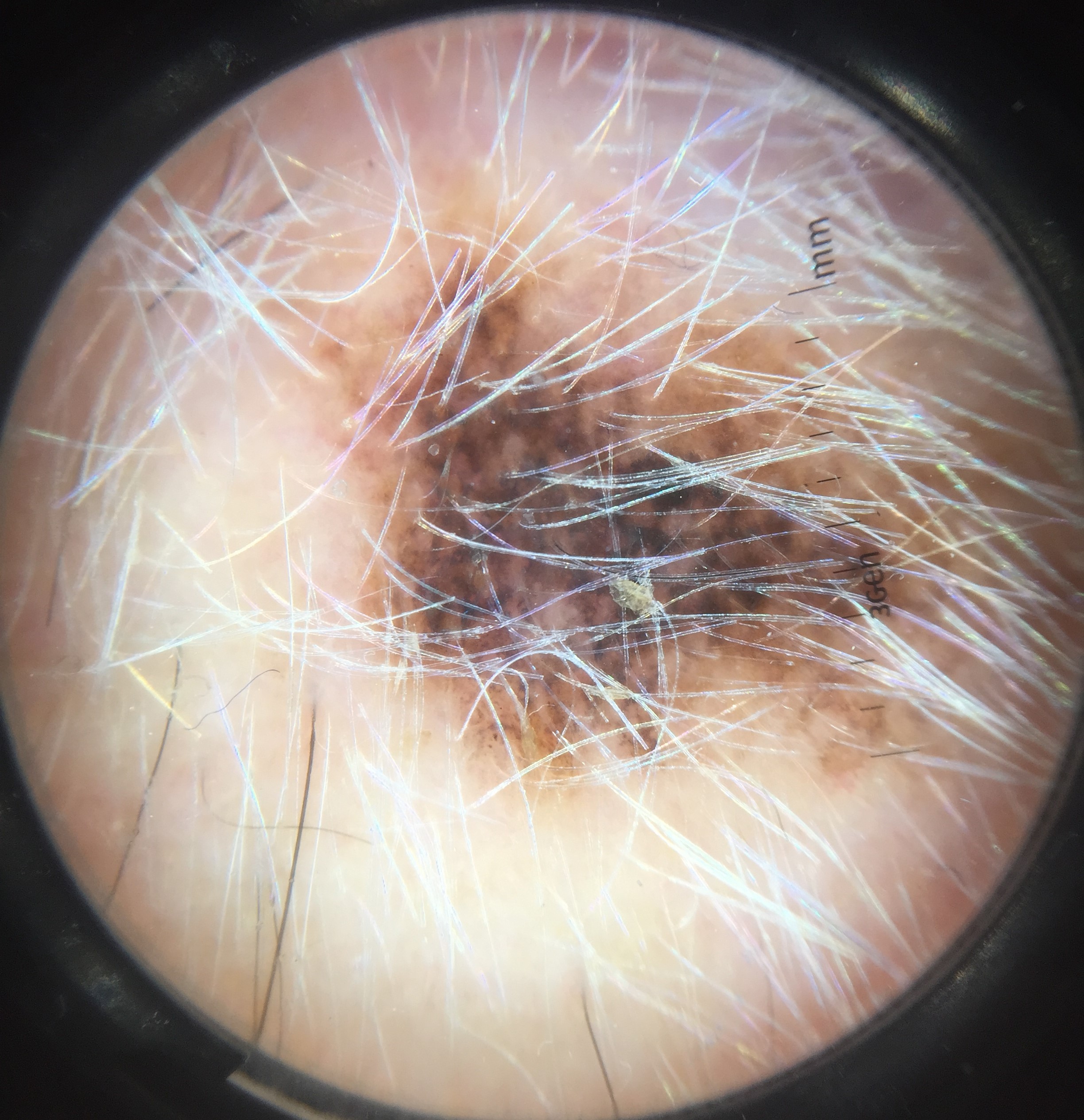image: dermoscopy
diagnosis:
  name: melanoma
  code: mel
  malignancy: malignant
  super_class: melanocytic
  confirmation: histopathology